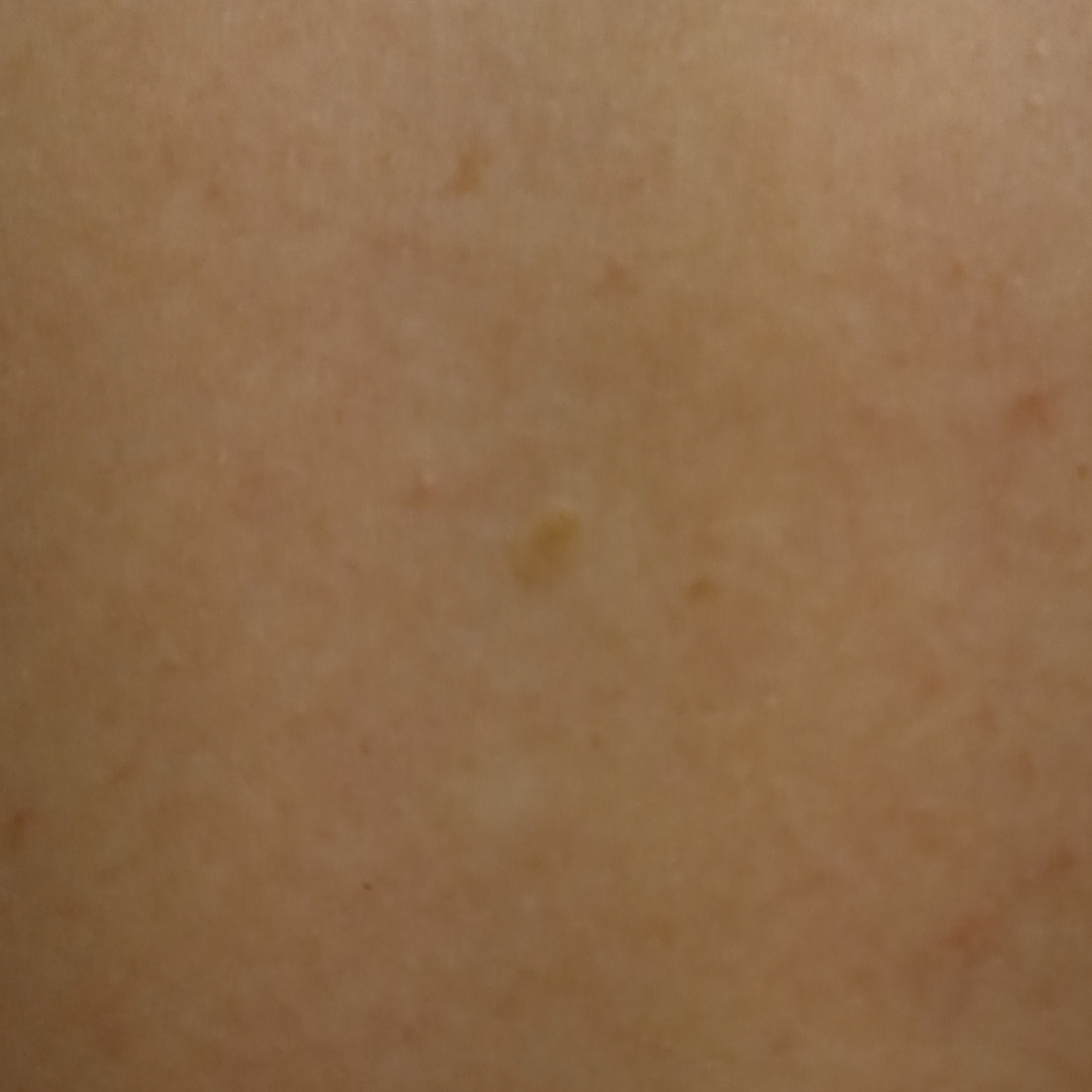patient:
  age: 48
  sex: female
image: clinical photo
referral: research study (no referral diagnosis)
lesion_location: the back
lesion_size:
  diameter_mm: 3.8
diagnosis:
  name: seborrheic keratosis
  malignancy: benign